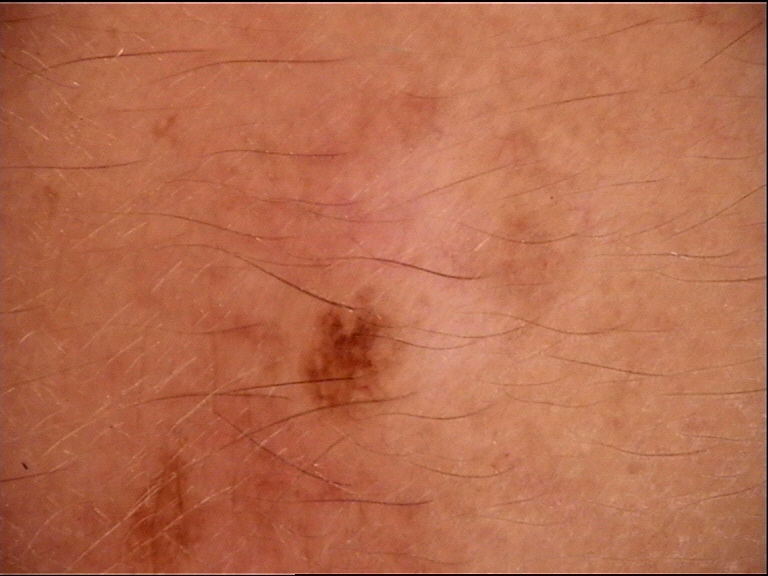Case:
* subtype — compound, banal
* diagnostic label — Miescher nevus (expert consensus)